A dermoscopic close-up of a skin lesion: 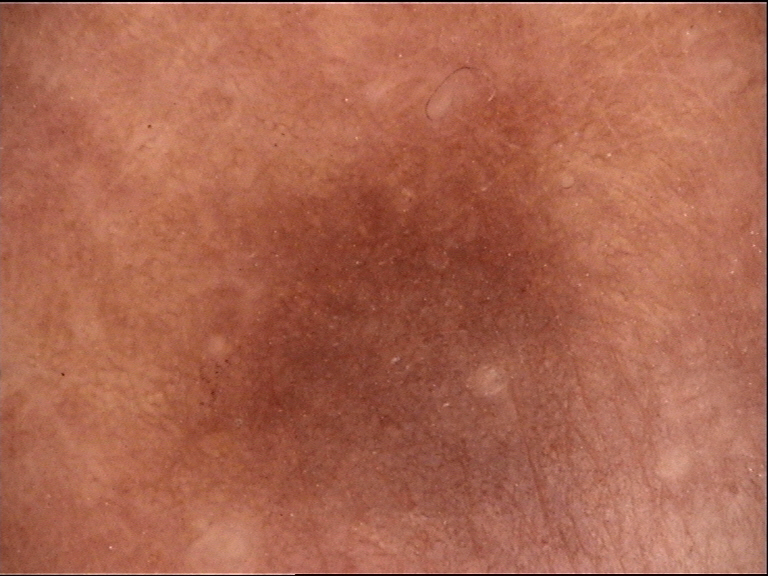{
  "lesion_type": {
    "main_class": "fibro-histiocytic"
  },
  "diagnosis": {
    "name": "dermatofibroma",
    "code": "df",
    "malignancy": "benign",
    "super_class": "non-melanocytic",
    "confirmation": "expert consensus"
  }
}